A dermatoscopic image of a skin lesion: 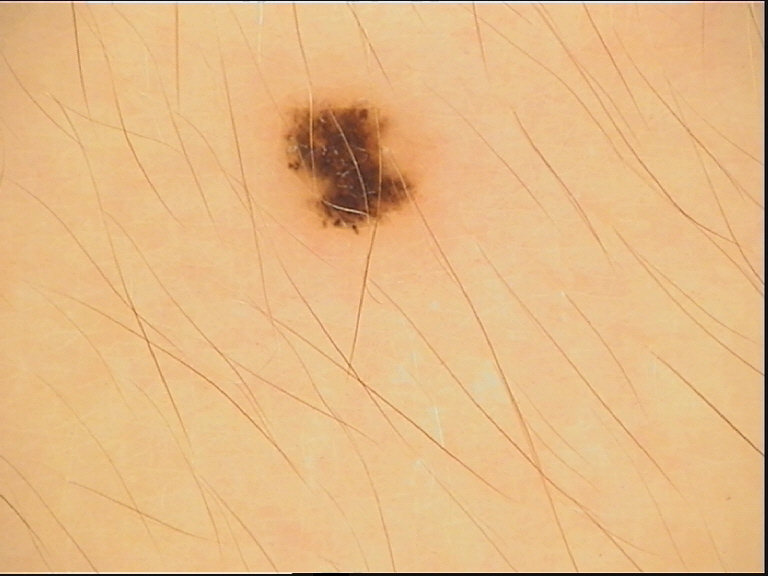diagnostic label: dysplastic junctional nevus (expert consensus).